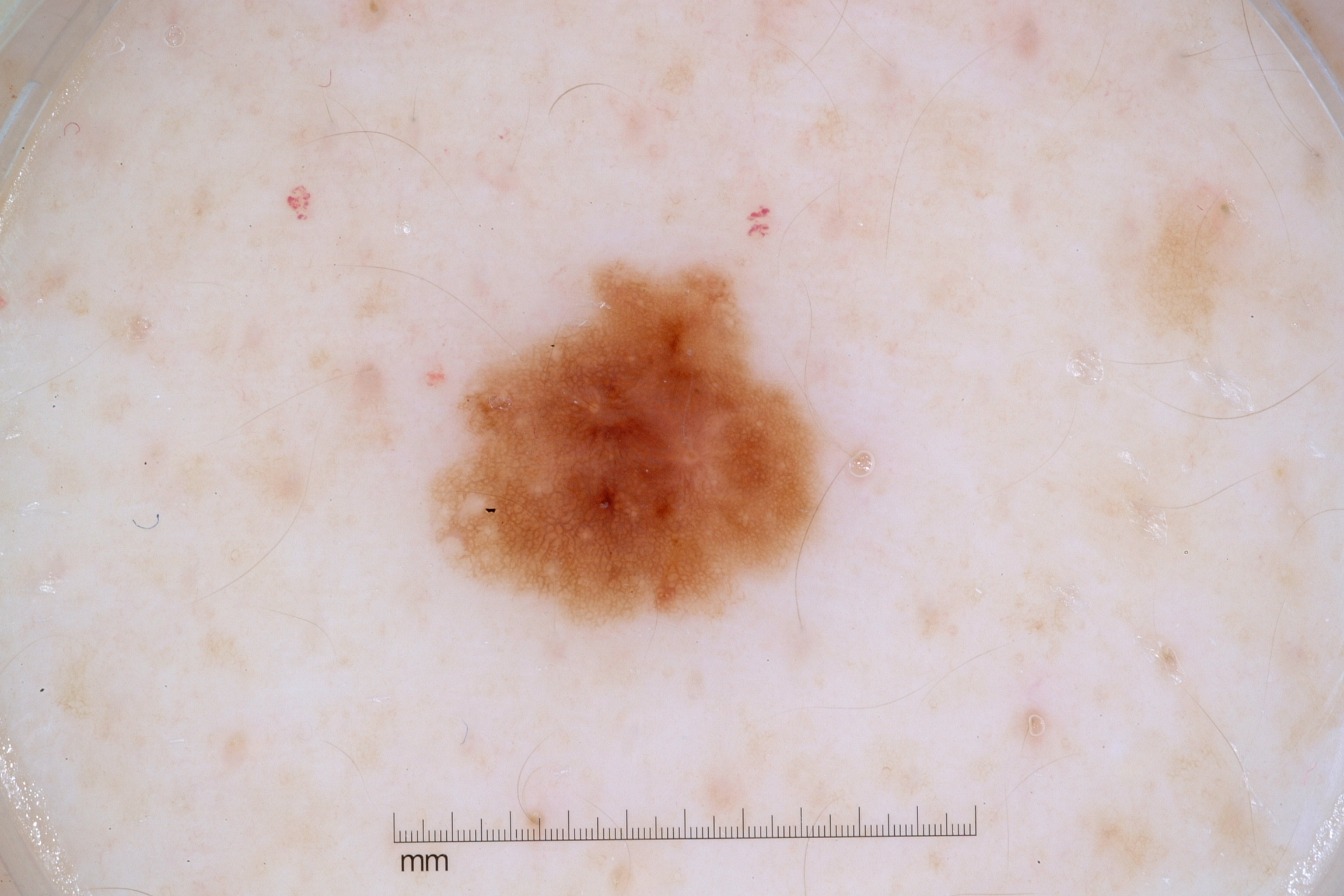The subject is a male about 45 years old.
A dermatoscopic image of a skin lesion.
Dermoscopically, the lesion shows milia-like cysts and pigment network.
With coordinates (x1, y1, x2, y2), the lesion spans [427,257,831,629].
Expert review diagnosed this as a melanocytic nevus.